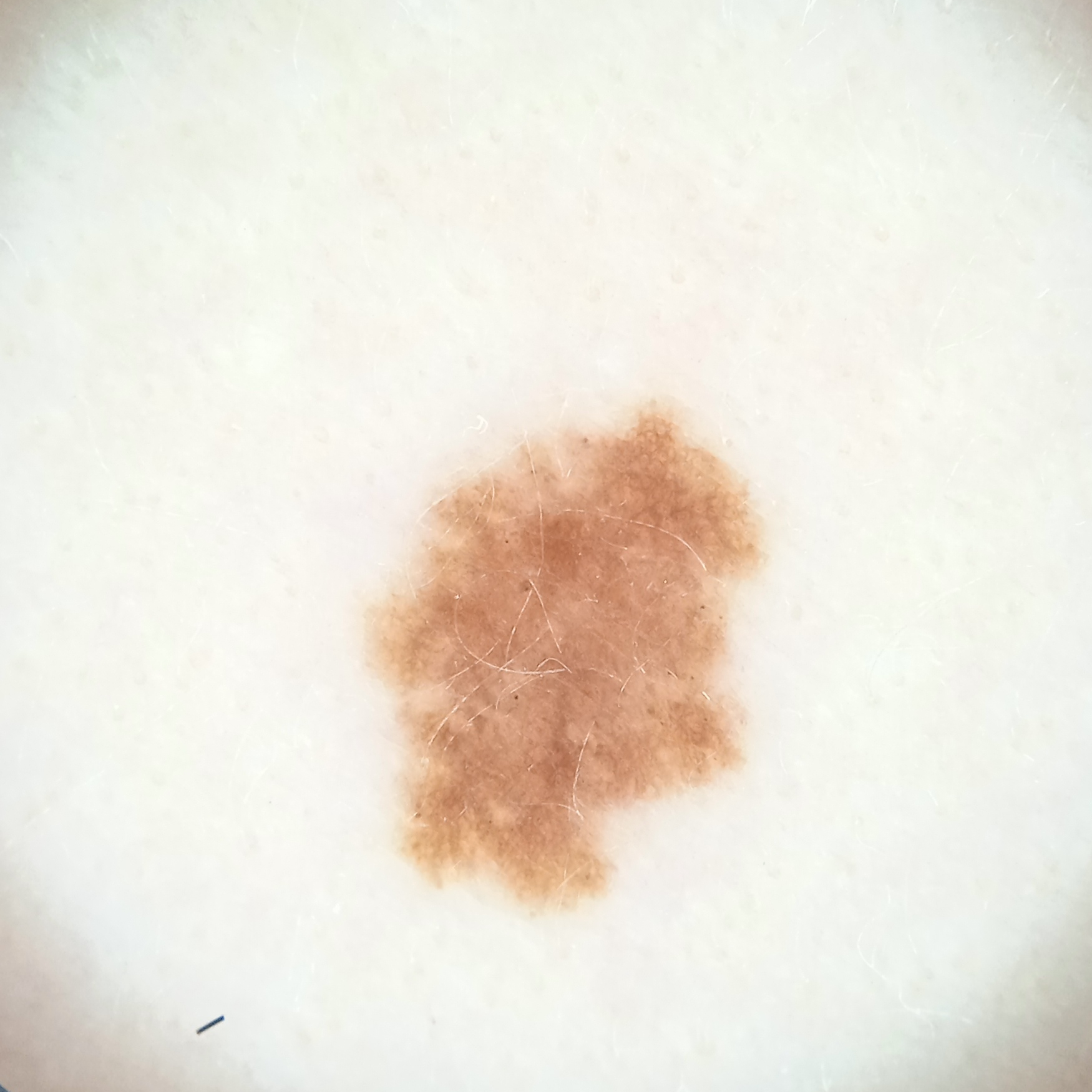| feature | finding |
|---|---|
| subject | female, age 27 |
| sun reaction | skin reddens with sun exposure |
| nevus count | a moderate number of melanocytic nevi |
| lesion size | 6.4 mm |
| diagnosis | atypical (dysplastic) nevus — dermatologist consensus |